The patient is female · the affected area is the leg · this is a close-up image — 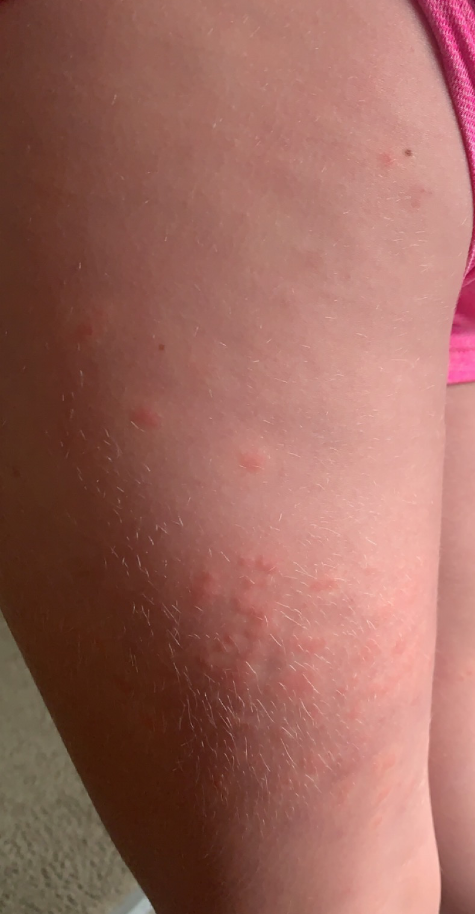assessment=Insect Bite (weight 0.50); Urticaria (weight 0.35); Allergic Contact Dermatitis (weight 0.15).